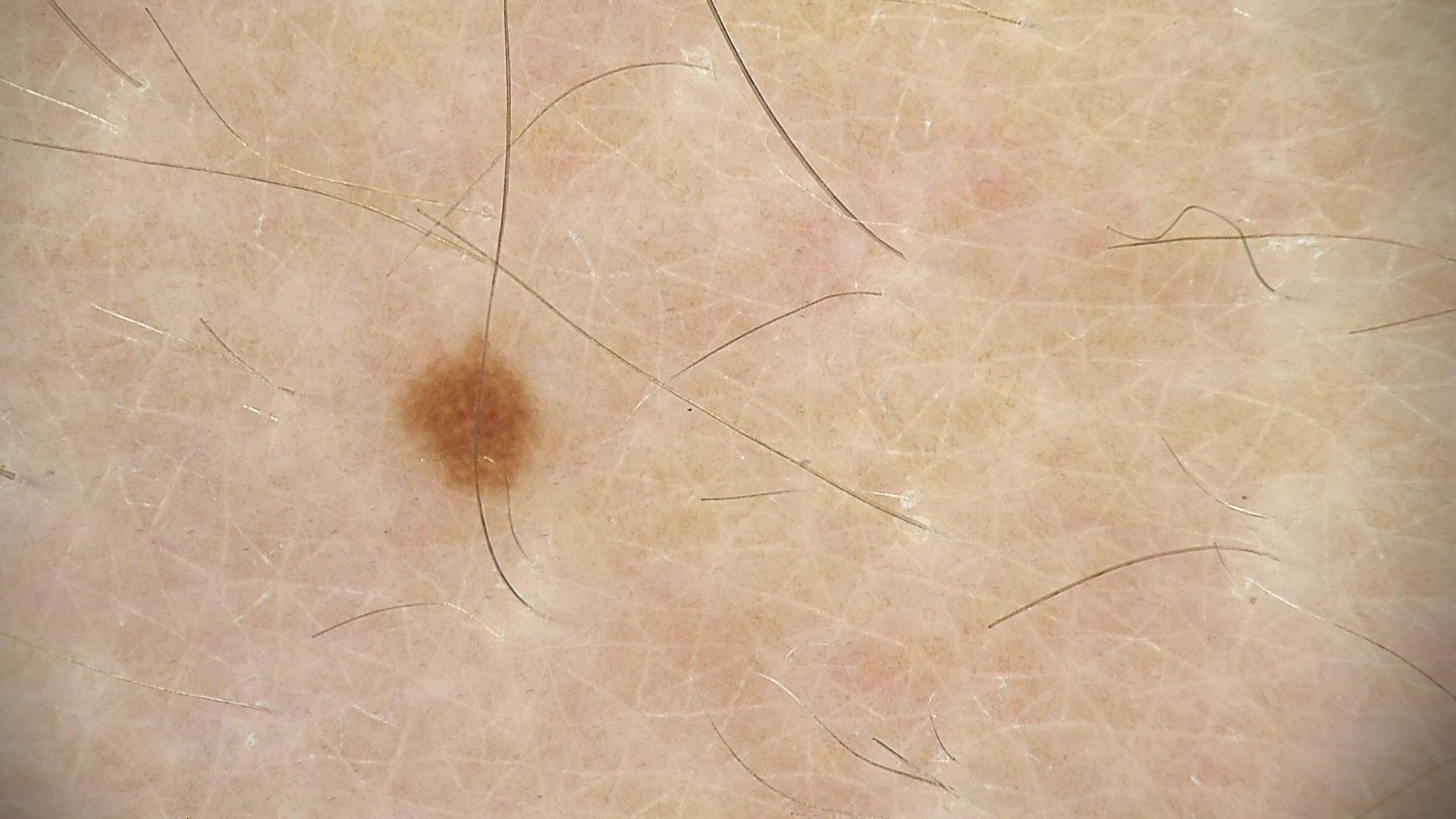Consistent with a dysplastic junctional nevus.